The photograph is a close-up of the affected area: 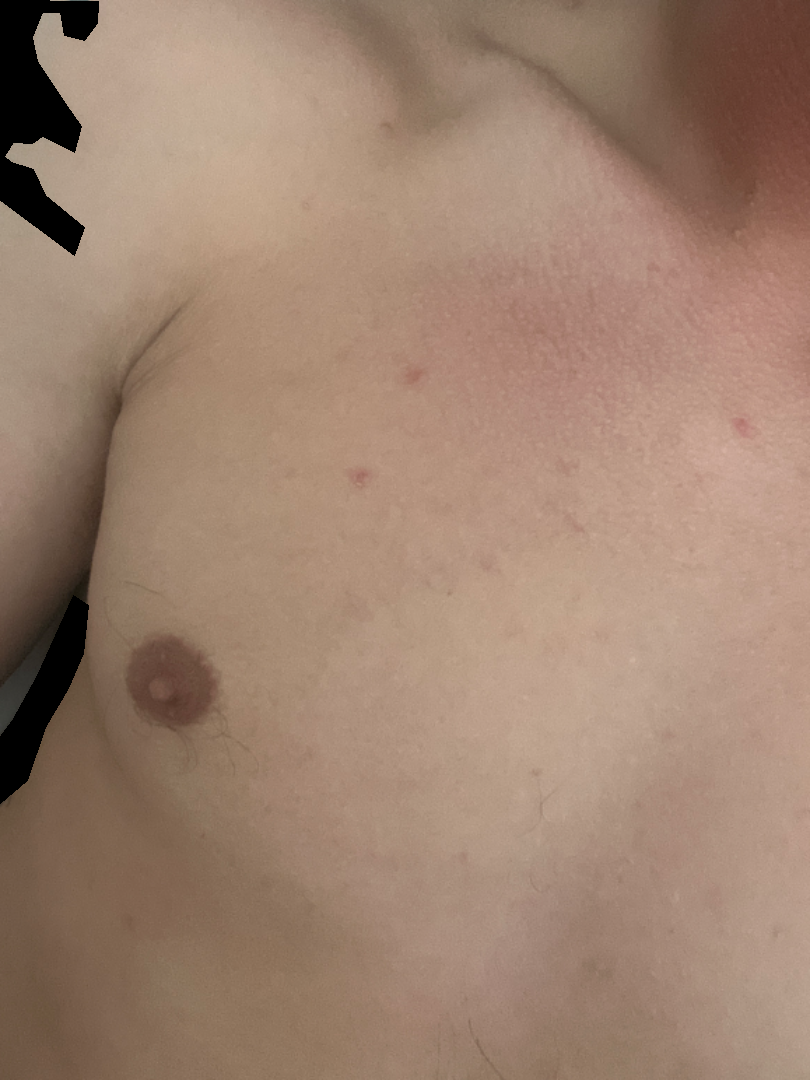One reviewing dermatologist: the primary impression is Folliculitis; the differential also includes Scabies; an alternative is Insect Bite.